A dermoscopic photograph of a skin lesion.
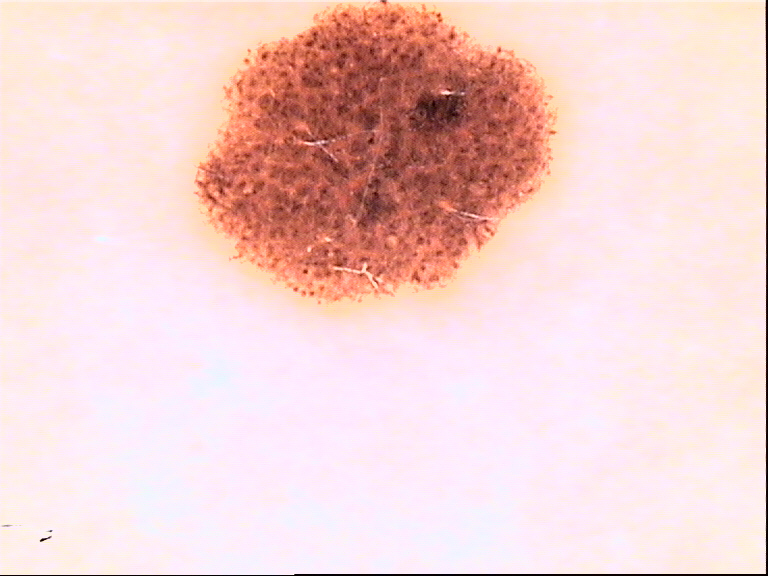The diagnostic label was a dysplastic junctional nevus.